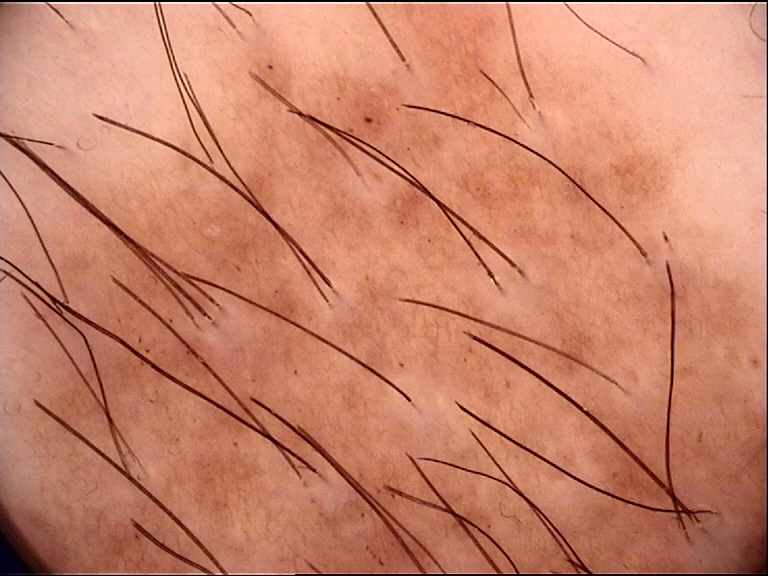image type: dermatoscopy, lesion type: banal, diagnostic label: congenital junctional nevus (expert consensus).